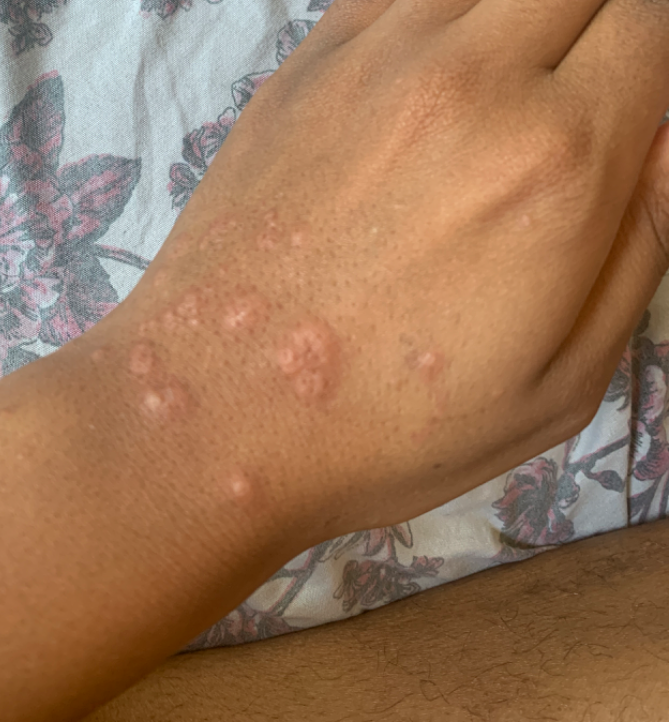<report>
<differential>
  <tied_lead>Diffuse xanthoma; Benign tumor of dermis; Insect Bite; Acute dermatitis, NOS; Collagenoma; Verruca vulgaris; Granulomatous disorder of the skin and subcutaneous tissue</tied_lead>
</differential>
</report>